Close-up view. The affected area is the front of the torso, leg and arm.
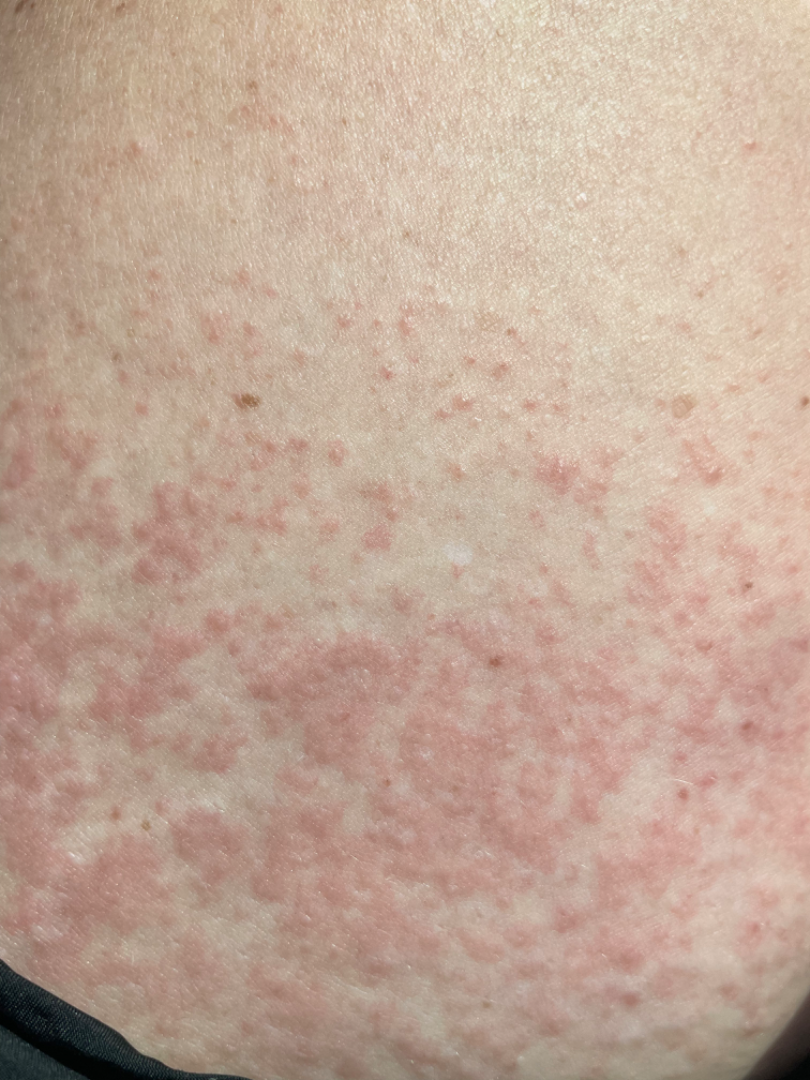The patient reports itching, bleeding, burning and pain. The lesion is described as raised or bumpy. The patient considered this a rash. Fitzpatrick phototype I. The patient reports associated fatigue and joint pain. The reviewing dermatologist's impression was: Morbilliform eruption (leading); Photodermatitis (possible); Urticaria (possible).